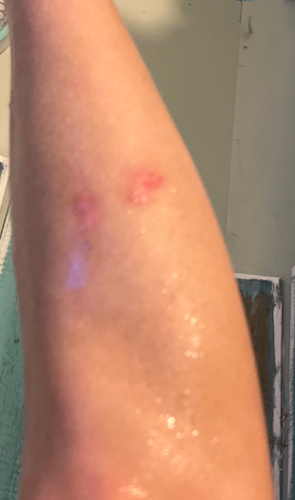Clinical context:
The patient described the issue as a rash. The lesion is described as rough or flaky. No relevant lesion symptoms reported. The affected area is the leg. No constitutional symptoms were reported. The contributor is a female aged 40–49. An image taken at a distance.
Assessment:
Reviewed remotely by one dermatologist: most consistent with Abrasion, scrape, or scab; an alternative is Burn erythema of lower leg.